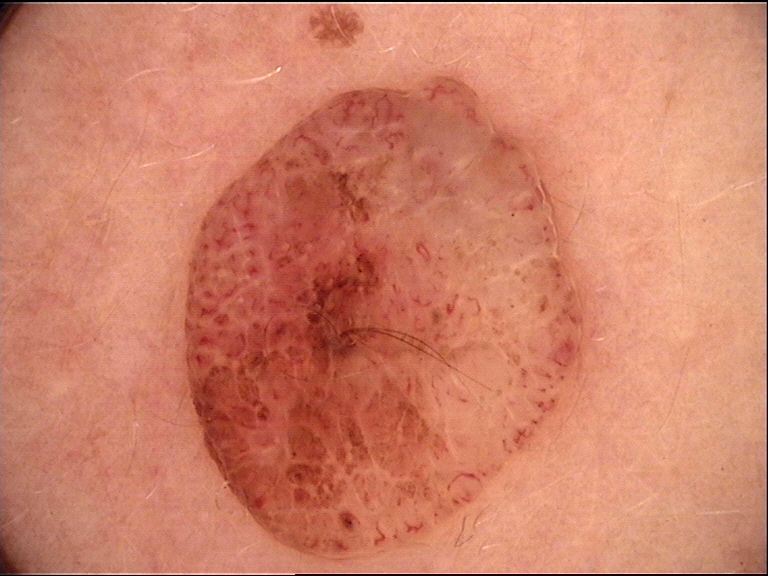A dermoscopic image of a skin lesion.
The morphology is that of a banal lesion.
The diagnosis was a dermal nevus.